Recorded as Fitzpatrick skin type II. A dermoscopic image of a skin lesion — 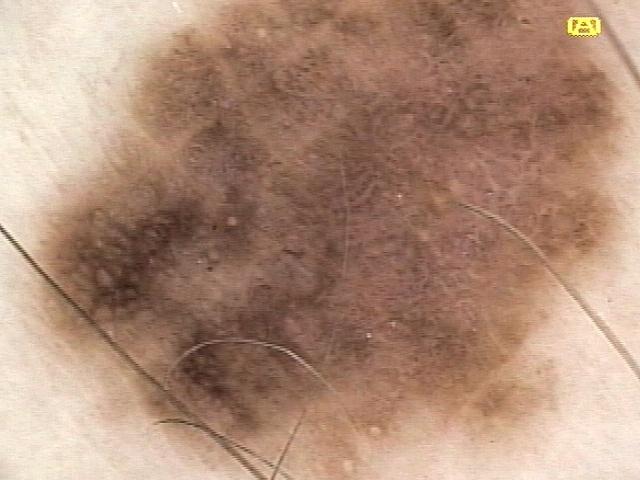Clinical context: The lesion is on a lower extremity. Diagnosis: Histopathology confirmed a melanoma.